This image was taken at a distance:
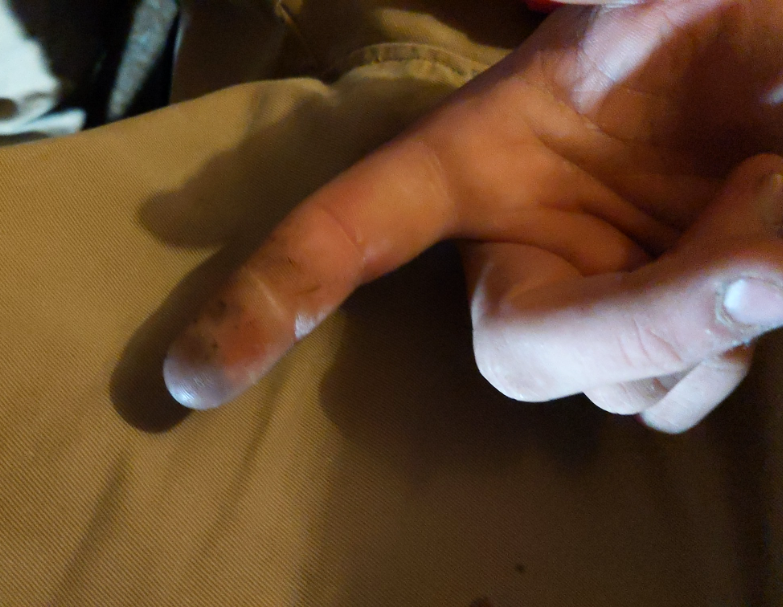Impression:
The reviewer was unable to grade this case for skin condition.